The patient is 40–49, female. Self-categorized by the patient as a rash. Reported duration is one to four weeks. The photo was captured at a distance. Located on the head or neck. The patient reported no systemic symptoms. The contributor notes the lesion is raised or bumpy:
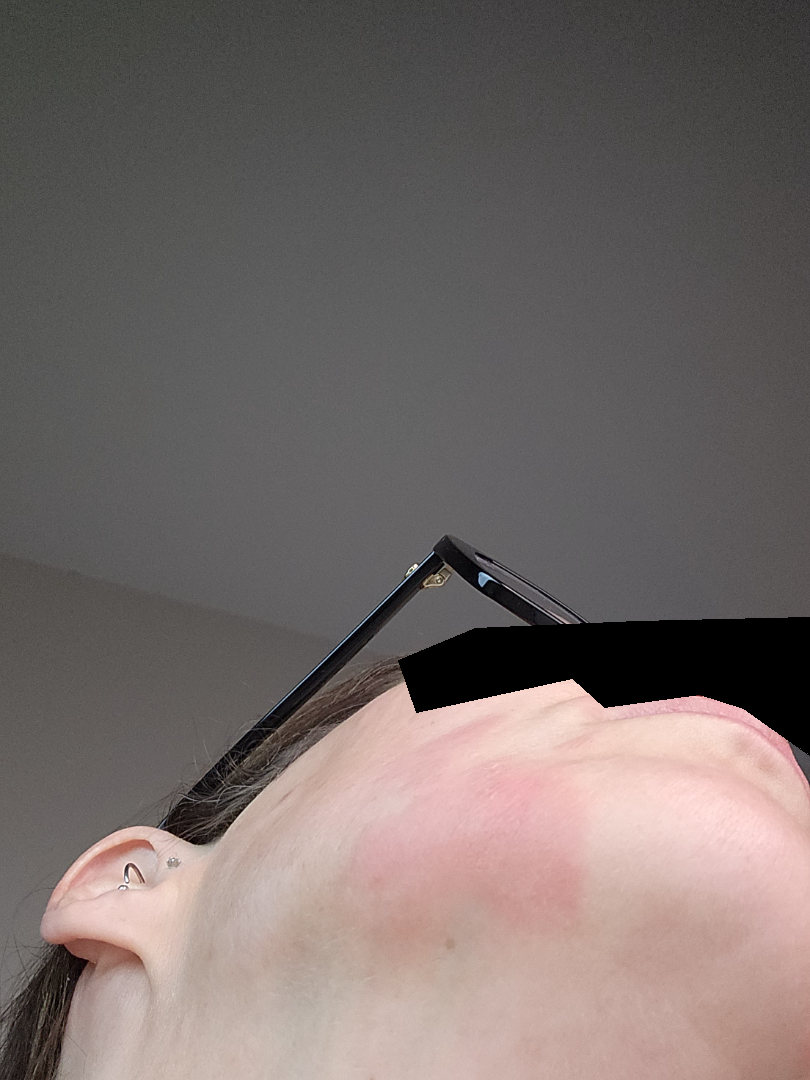The image was not sufficient for the reviewer to characterize the skin condition.